A male subject, a dermoscopic close-up of a skin lesion: 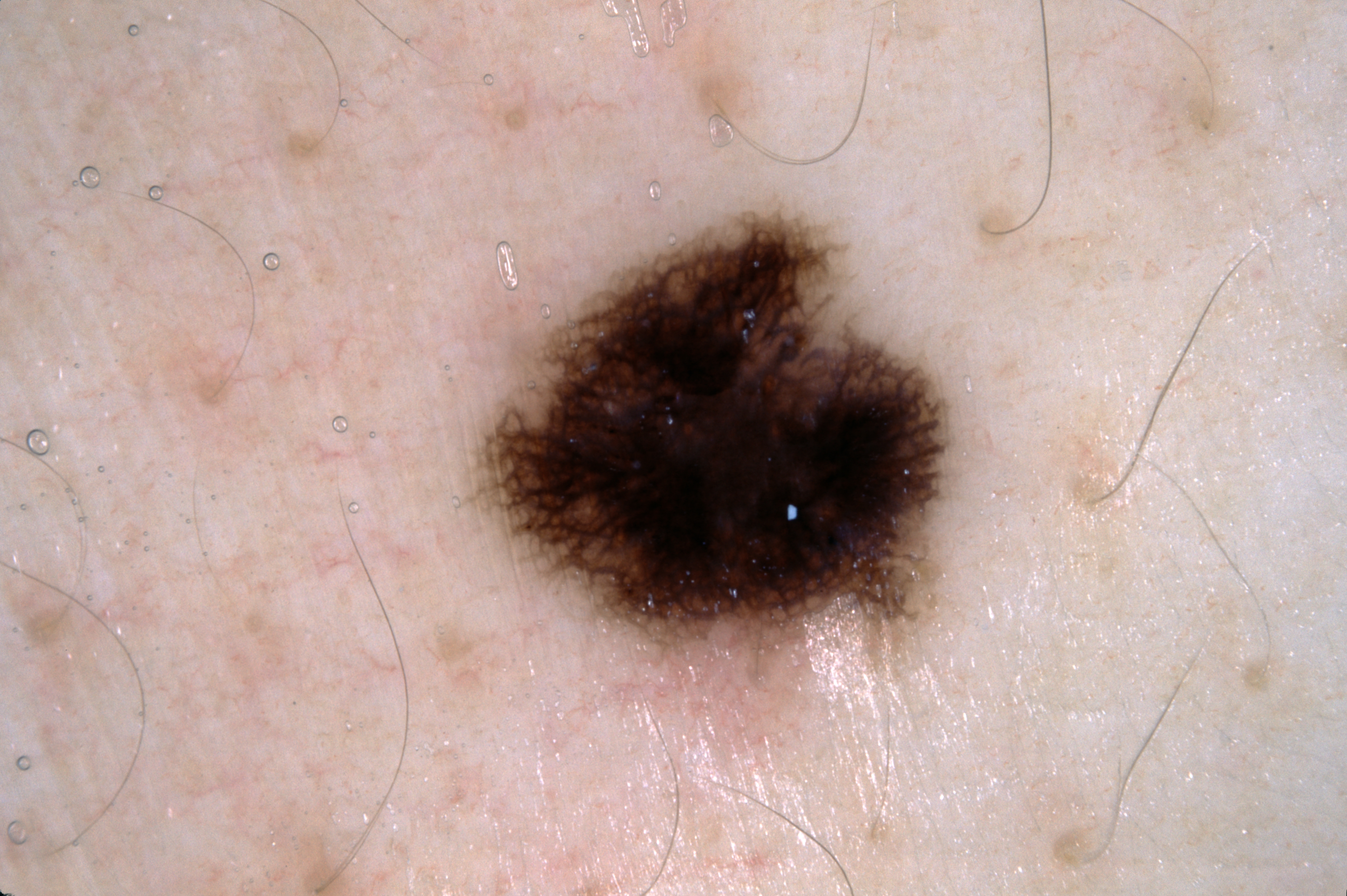Image and clinical context: Dermoscopically, the lesion shows pigment network; no milia-like cysts, streaks, or negative network. With coordinates (x1, y1, x2, y2), the lesion is bounded by 467 209 954 682. Conclusion: Expert review diagnosed this as a melanocytic nevus.